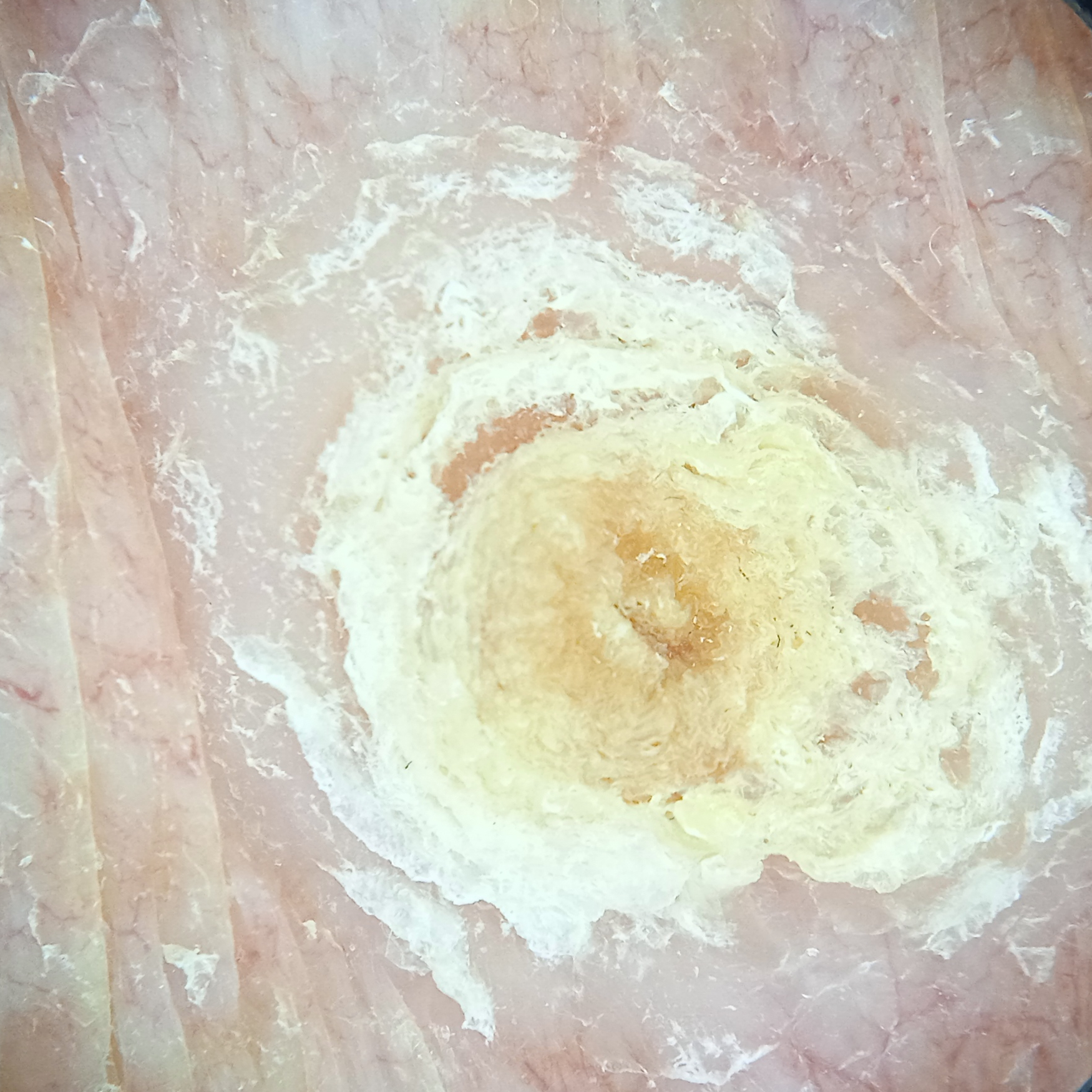| feature | finding |
|---|---|
| risk factors | a personal history of cancer, a family history of skin cancer |
| sun reaction | skin tans without first burning |
| subject | female, age 92 |
| image type | dermoscopy |
| clinical context | research study (no referral diagnosis) |
| location | the torso |
| lesion size | 12.5 mm |
| diagnosis | squamous cell carcinoma (dermatologist consensus) |